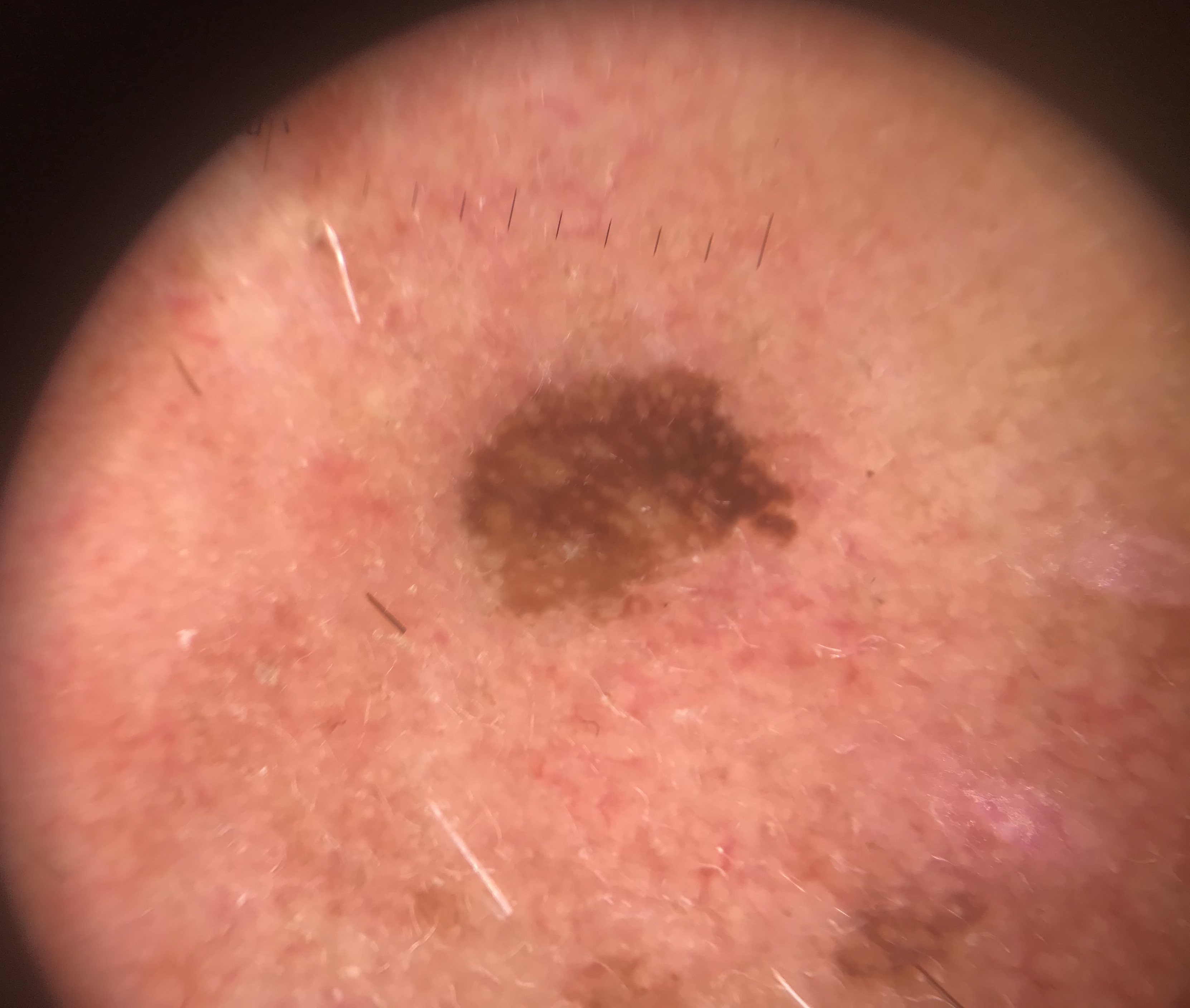This is a keratinocytic lesion. Diagnosed as a seborrheic keratosis.